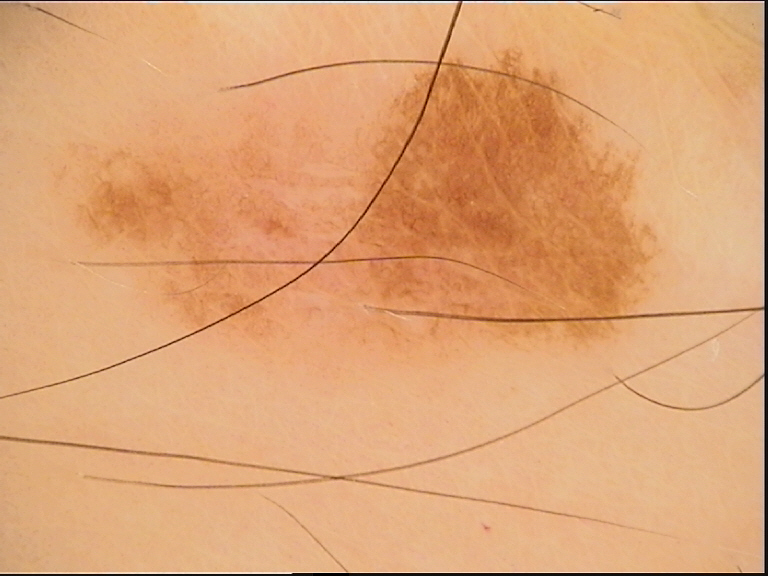Conclusion: Labeled as a dysplastic junctional nevus.